The photo was captured at a distance · the affected area is the leg · the patient is a male aged 40–49: 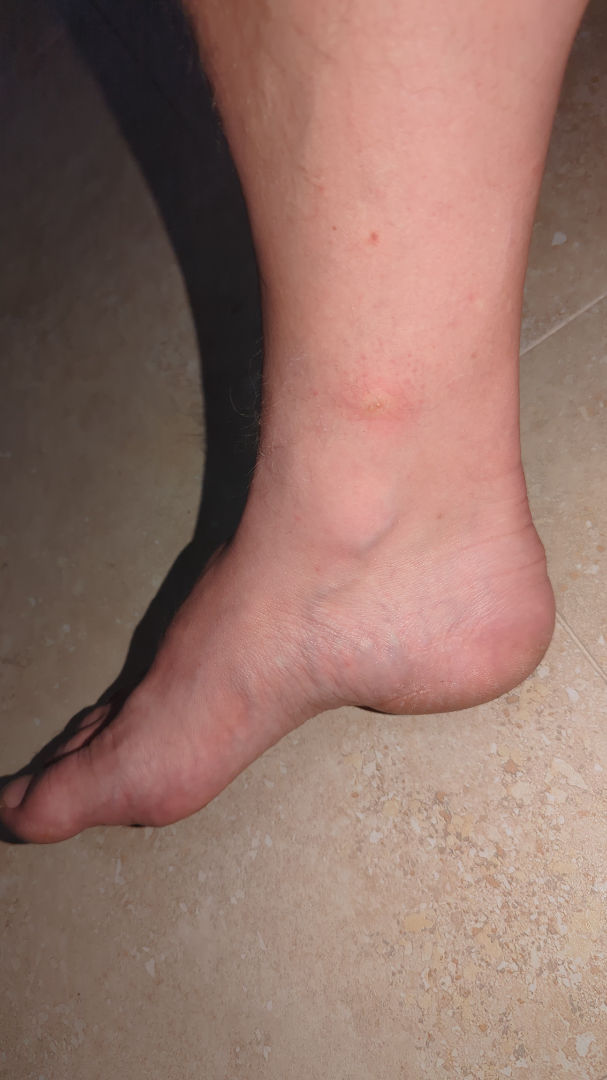* differential — the leading consideration is Insect Bite; less likely is Erythema migrans; less probable is Impetigo; a remote consideration is Drug Rash; a more distant consideration is Allergic Contact Dermatitis; lower on the differential is Abscess